An image taken at an angle:
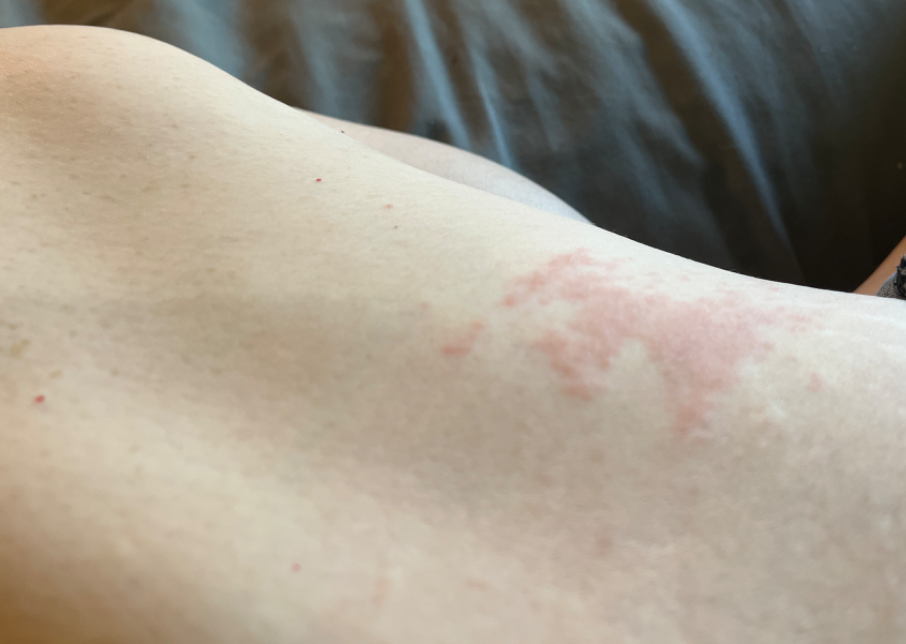One reviewing dermatologist: Acute dermatitis, NOS and Irritant Contact Dermatitis were each considered, in no particular order.